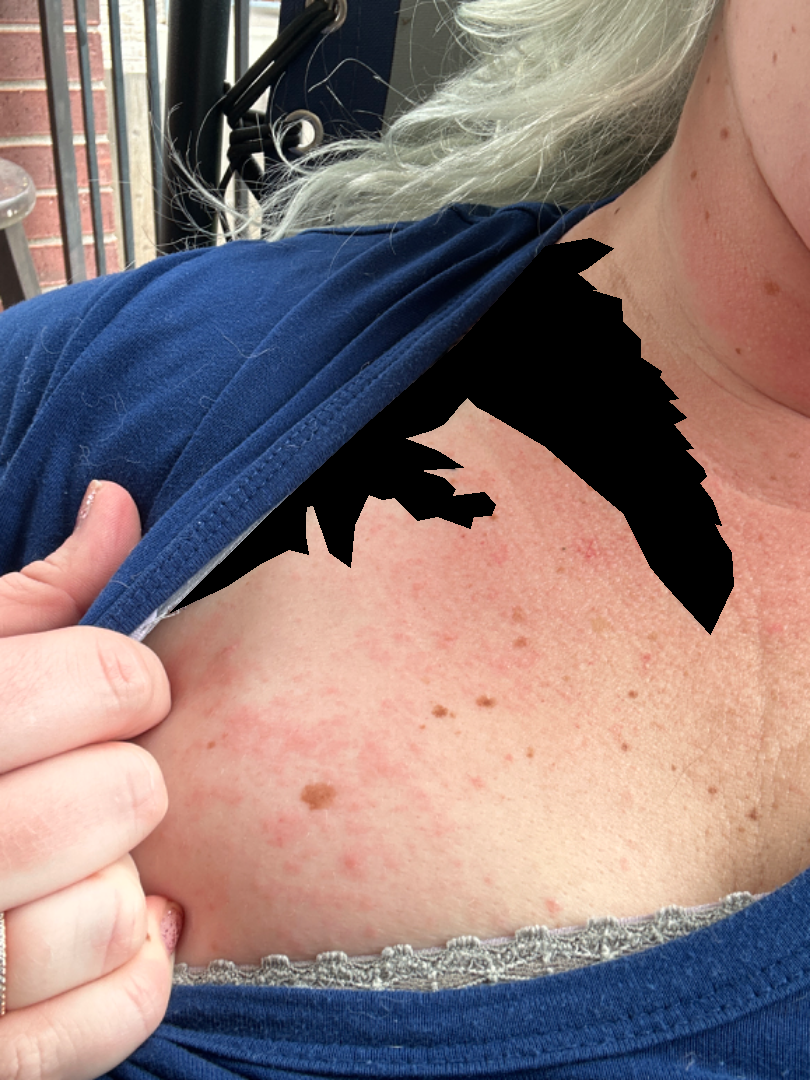shot type — close-up; history — less than one week; body site — front of the torso, leg and arm; texture — raised or bumpy; patient's own categorization — a rash; subject — female, age 30–39; patient-reported symptoms — enlargement, bothersome appearance and itching.